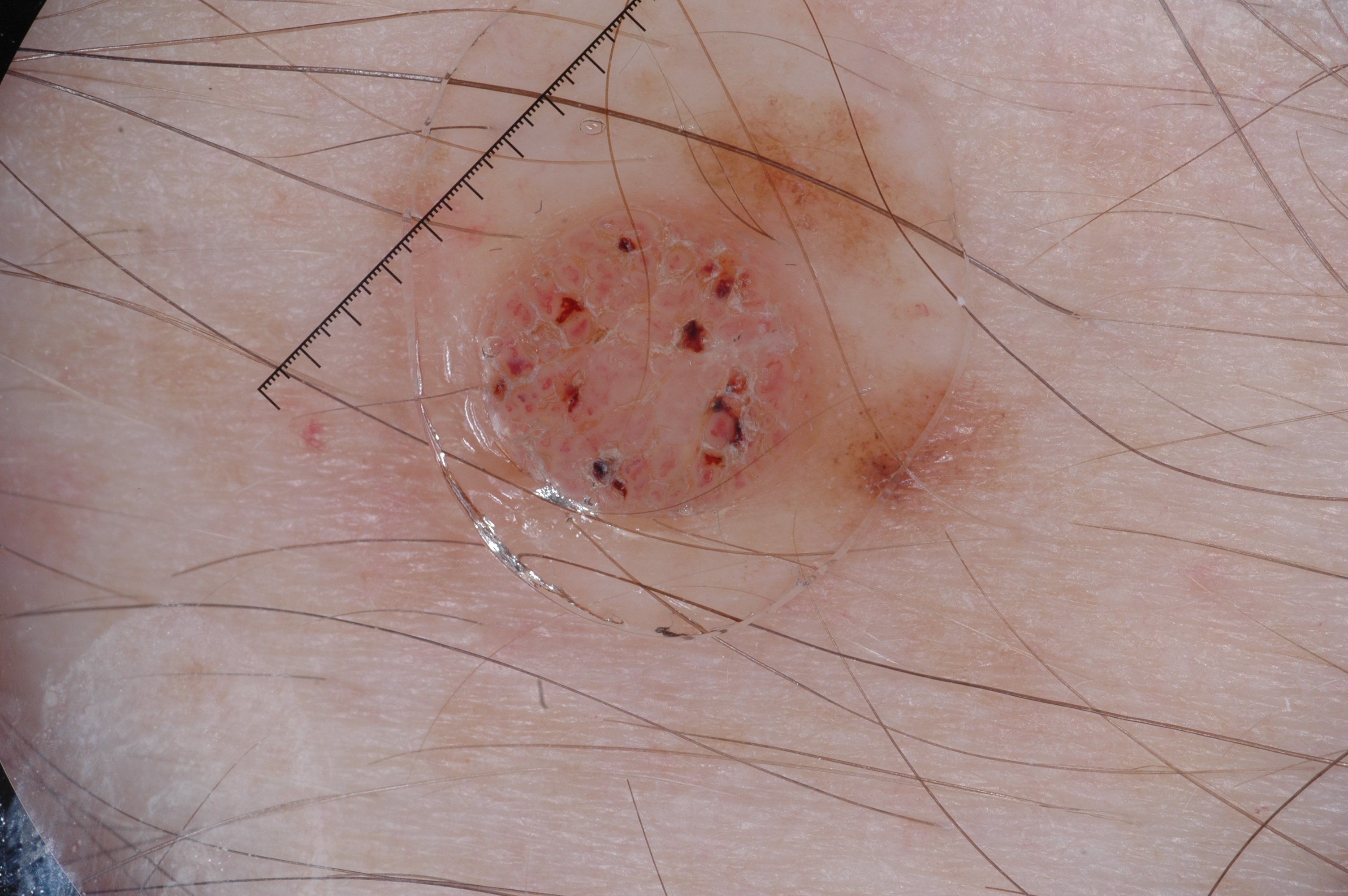The subject is a male aged 63 to 67. A dermoscopic image of a skin lesion. The lesion is located at x1=465 y1=75 x2=993 y2=543. Dermoscopically, the lesion shows milia-like cysts and pigment network, with no streaks or negative network. Diagnosed as a seborrheic keratosis.